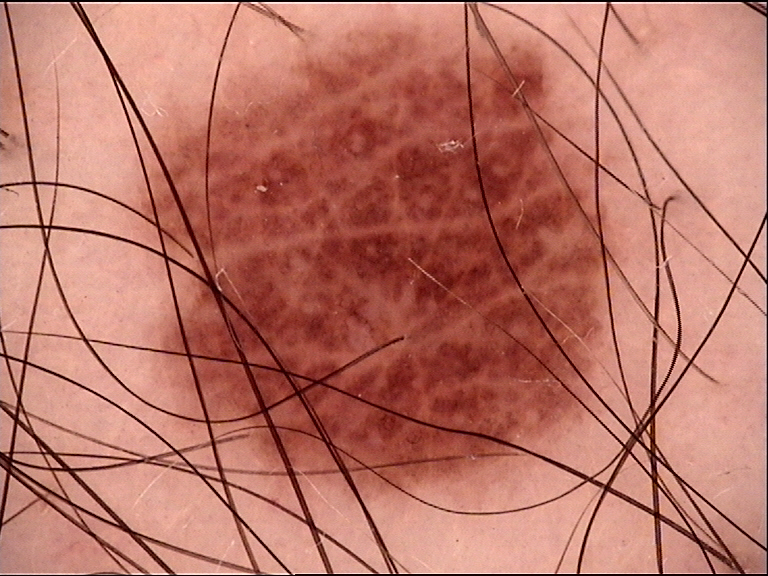The diagnostic label was a dysplastic junctional nevus.